The condition has been present for less than one week. The lesion is described as raised or bumpy. The lesion involves the front of the torso, arm, back of the torso and head or neck. No constitutional symptoms were reported. The photo was captured at an angle. Symptoms reported: itching: 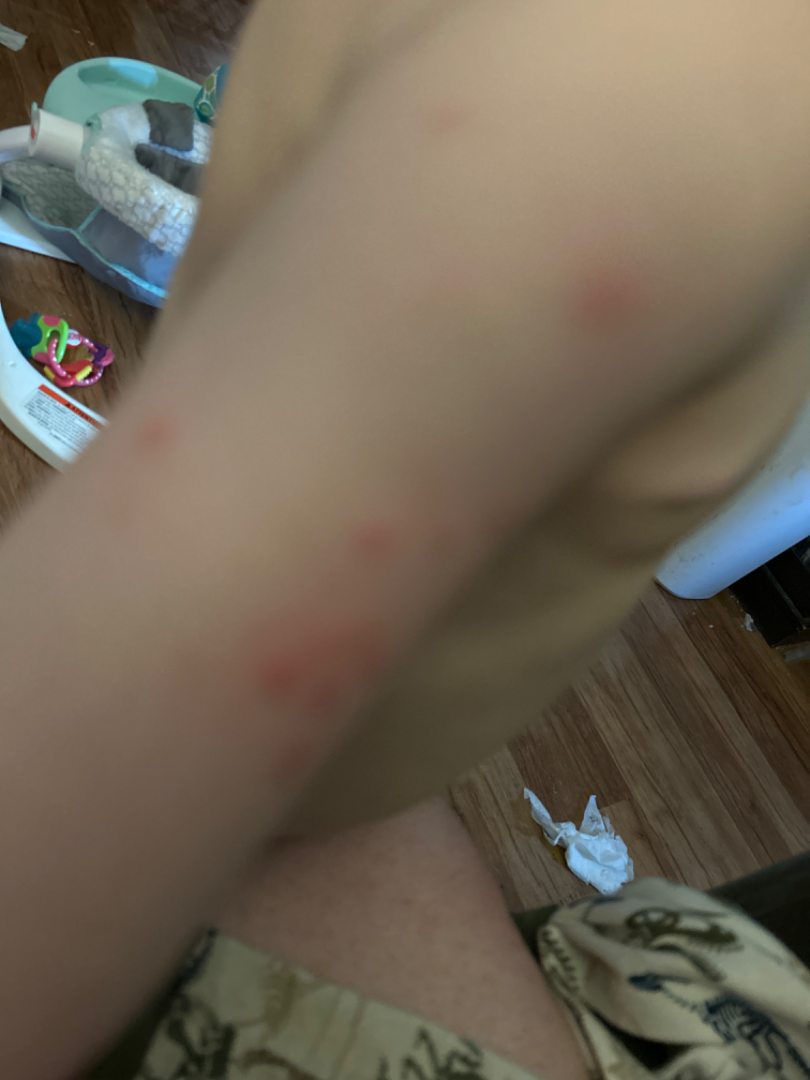assessment: indeterminate.